A clinical photograph showing a skin lesion.
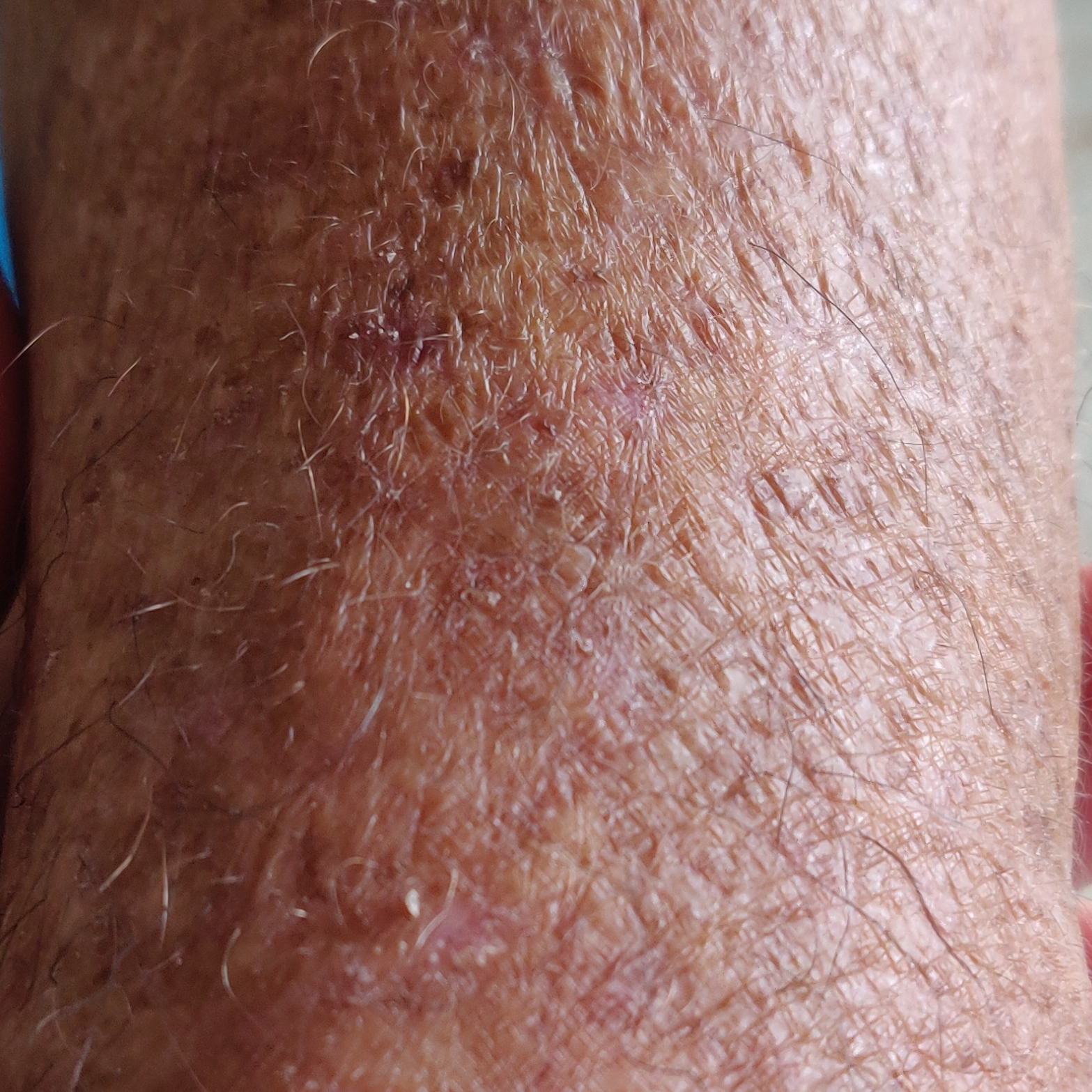Clinical context:
The lesion is located on a forearm. The patient describes that the lesion has changed and itches, but does not hurt.
Conclusion:
Consistent with an actinic keratosis.